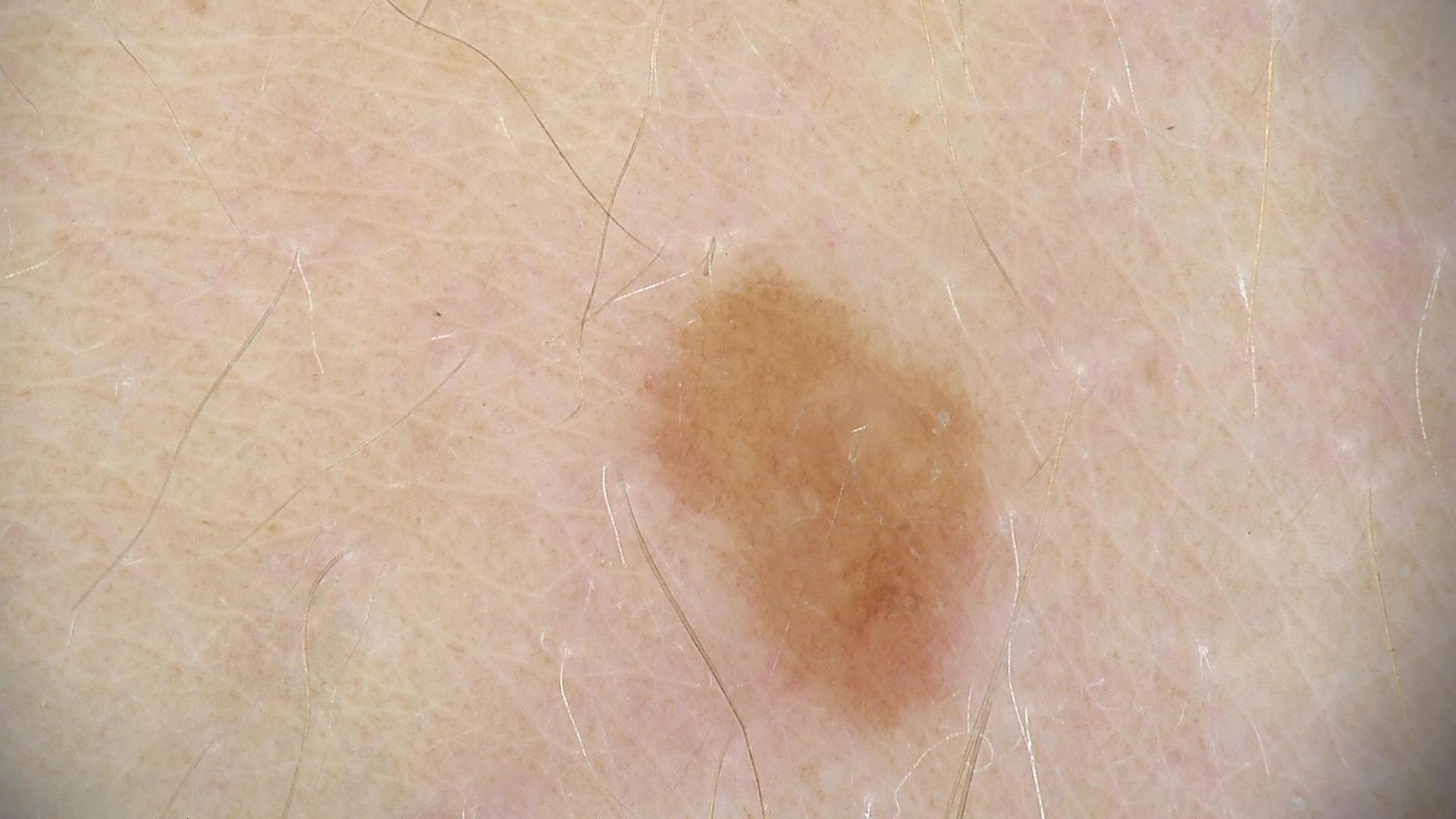diagnostic label=compound nevus (expert consensus)